Reported lesion symptoms include burning and itching, skin tone: Fitzpatrick phototype II; lay reviewers estimated MST 2 or 3 (two reviewer pools), the contributor is a female aged 18–29, the photograph is a close-up of the affected area, the leg is involved: 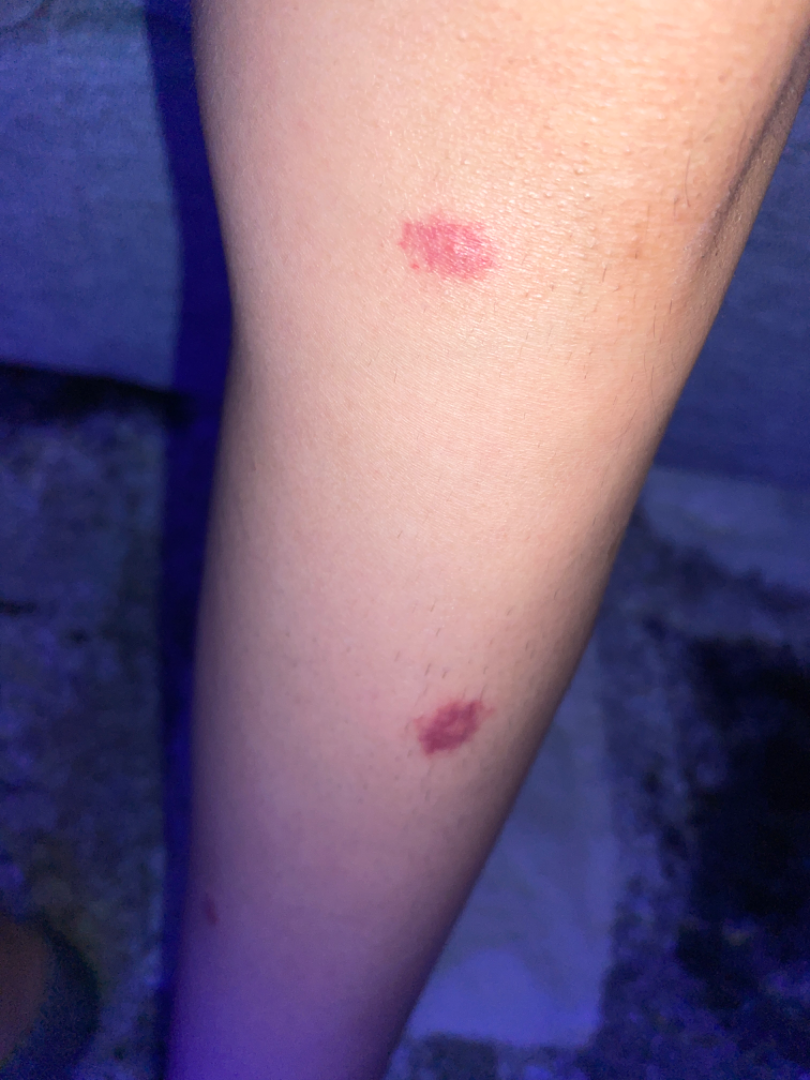differential:
  leading:
    - Insect Bite
  considered:
    - Pigmented purpuric eruption
  unlikely:
    - Leukemia cutis